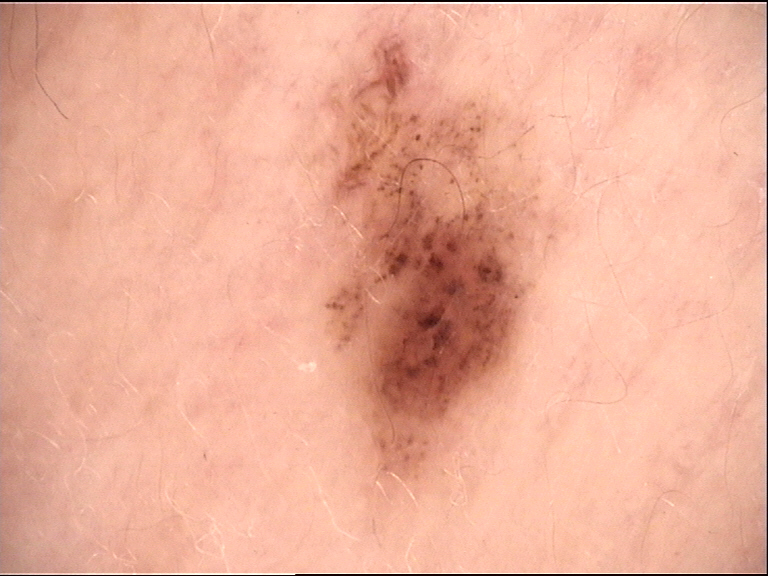A skin lesion imaged with a dermatoscope. Diagnosed as a dysplastic compound nevus.